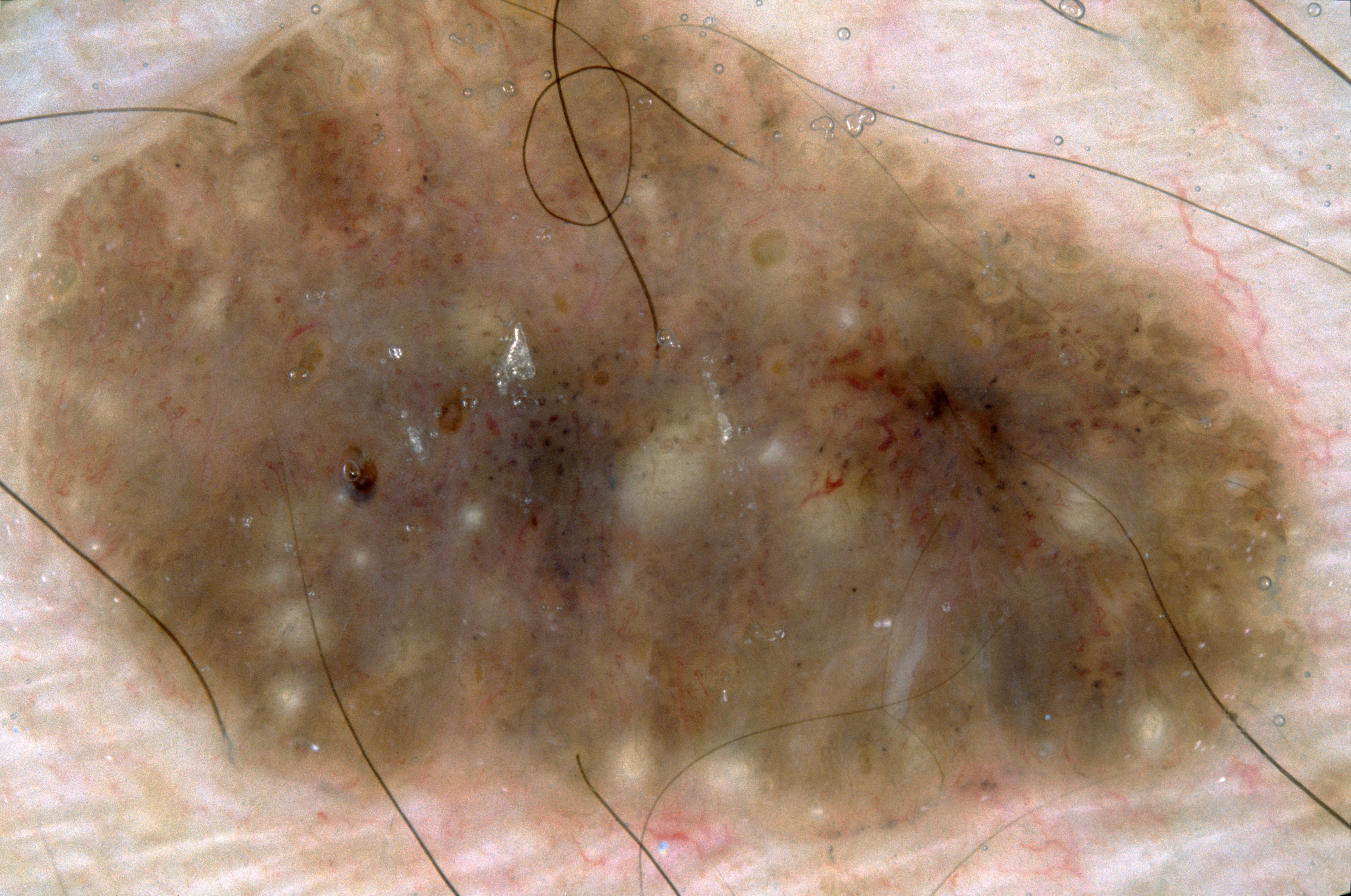Findings:
A dermatoscopic image of a skin lesion. Dermoscopic review identifies milia-like cysts; no negative network, pigment network, or streaks. The lesion extends across almost the whole field of view.
Conclusion:
The lesion was assessed as a seborrheic keratosis.